A dermoscopic image of a skin lesion.
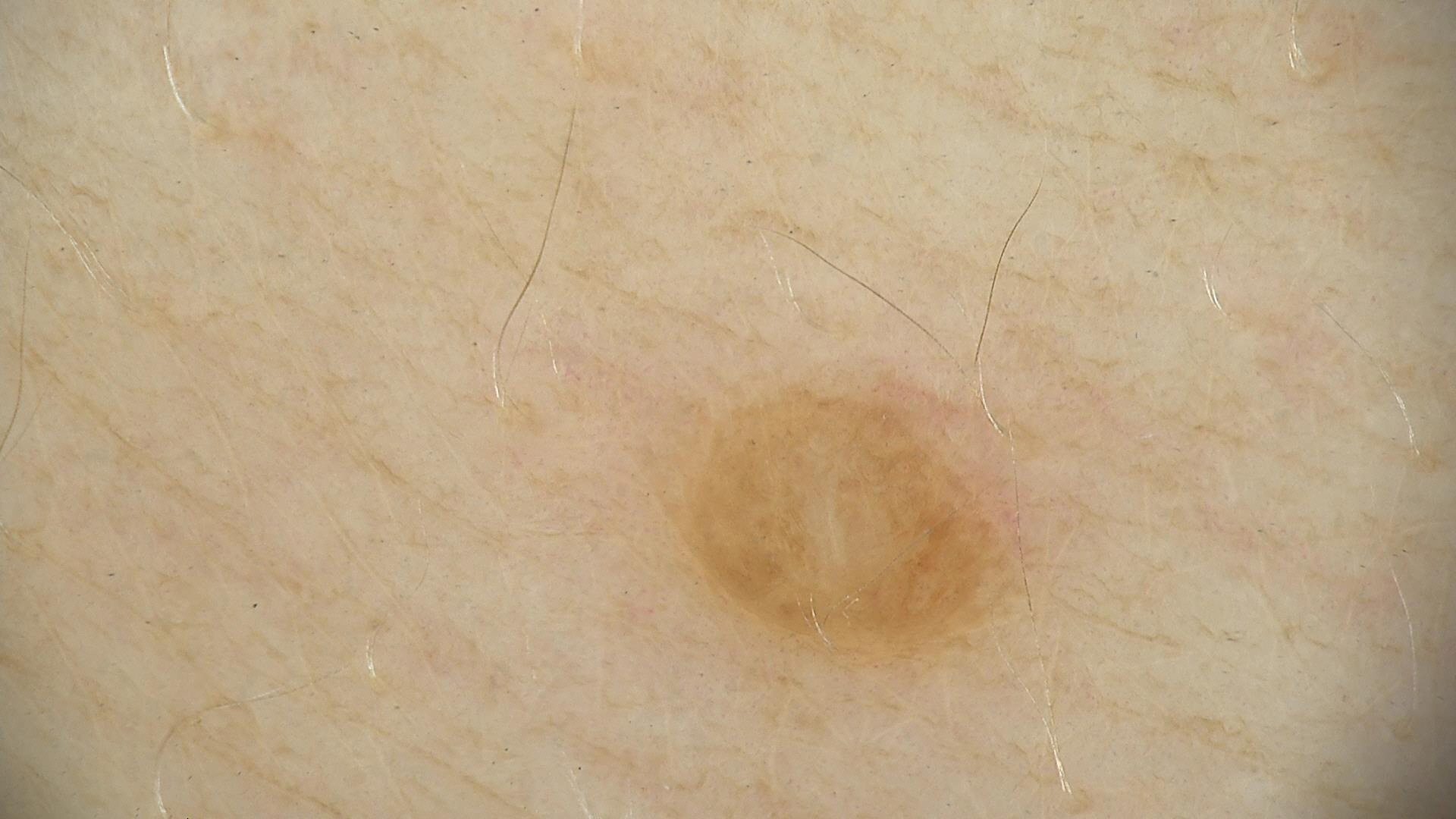Conclusion:
The diagnosis was a banal lesion — a dermal nevus.